The patient considered this a rash. Located on the front of the torso, back of the torso, arm, head or neck and leg. The patient reports the condition has been present for more than one year. Close-up view. The patient reports the lesion is rough or flaky. The patient is a female aged 50–59 — 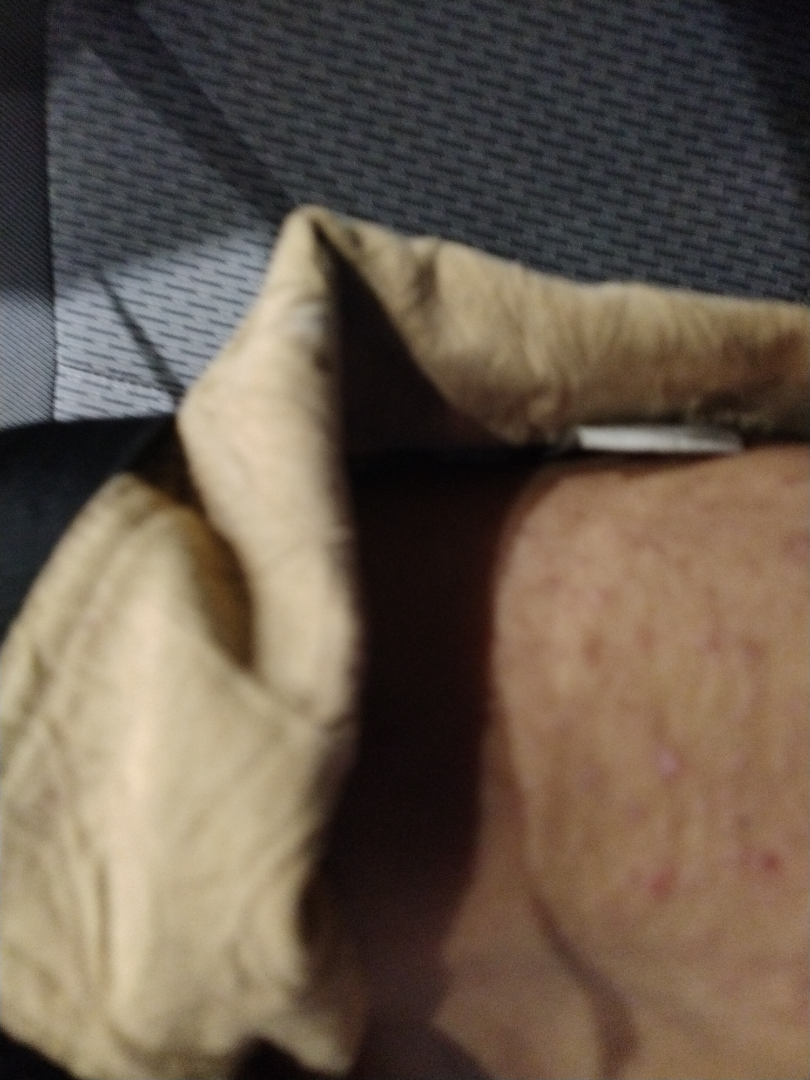Case summary:
• clinical impression: Lichen Simplex Chronicus (most likely); Eczema (considered)